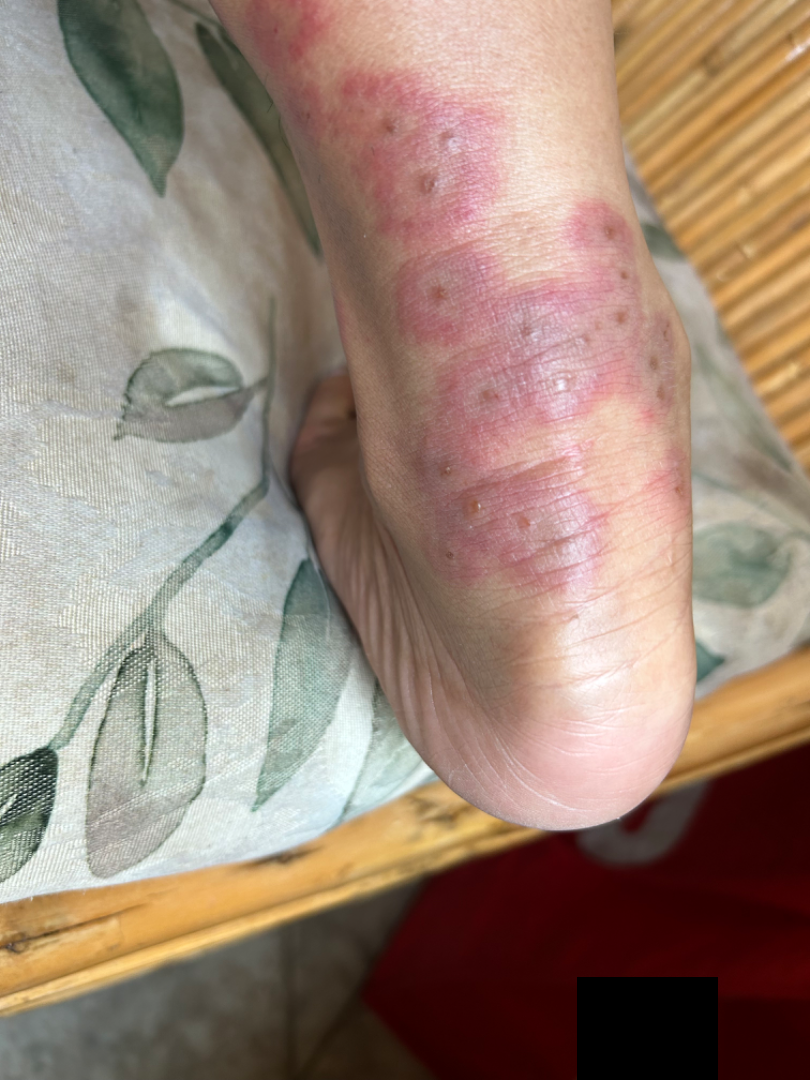A close-up photograph. The patient considered this a rash. The leg and arm are involved. Symptoms reported: bothersome appearance, pain and itching. On remote review of the image, the leading consideration is Erythema multiforme; an alternative is Insect Bite; less likely is Leukocytoclastic Vasculitis; less probable is Drug Rash.